Symptoms reported: itching, enlargement, bothersome appearance and darkening · this is a close-up image · located on the head or neck · the patient considered this a rash · the lesion is described as raised or bumpy and rough or flaky · skin tone: Fitzpatrick V; non-clinician graders estimated a MST of 7 — 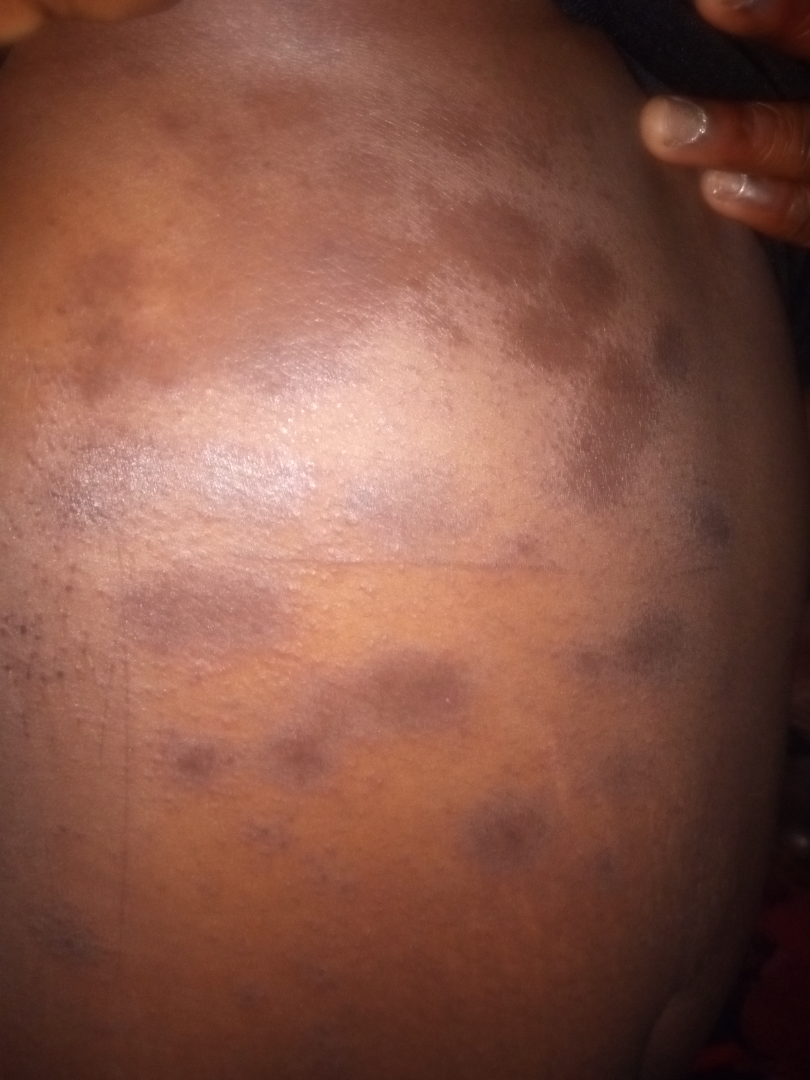assessment: indeterminate